This is a close-up image:
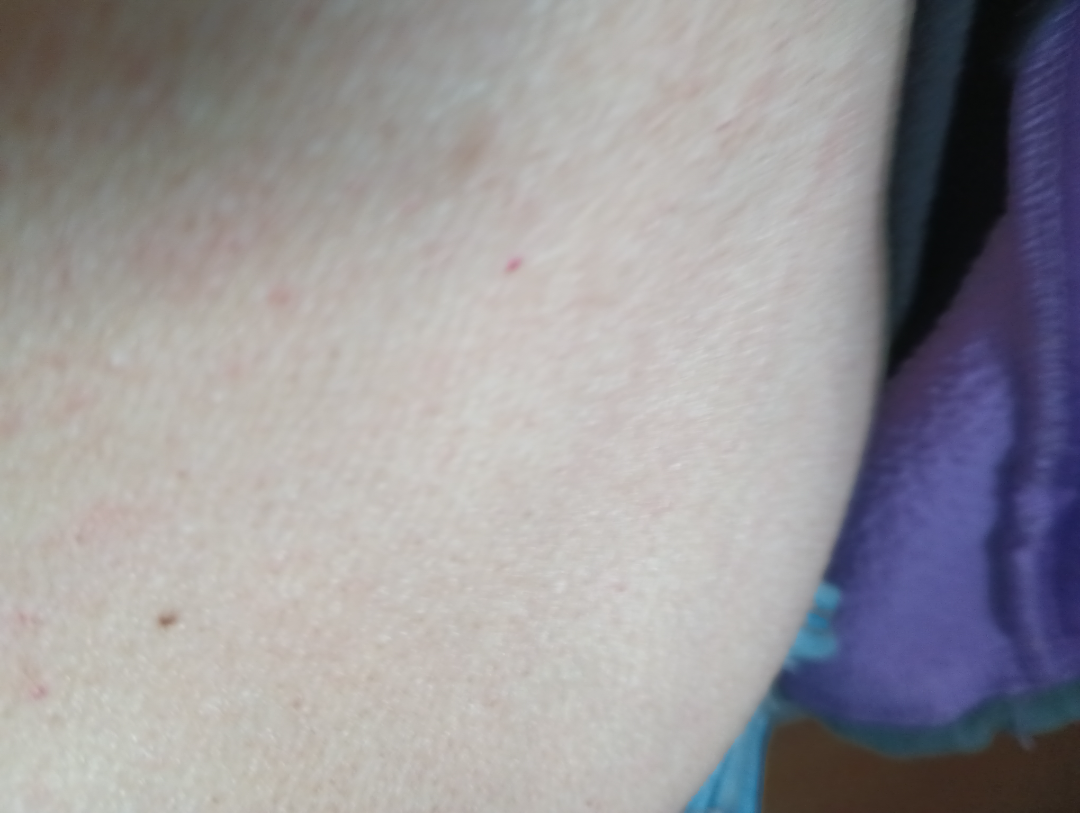The case was indeterminate on photographic review.